A dermatoscopic image of a skin lesion.
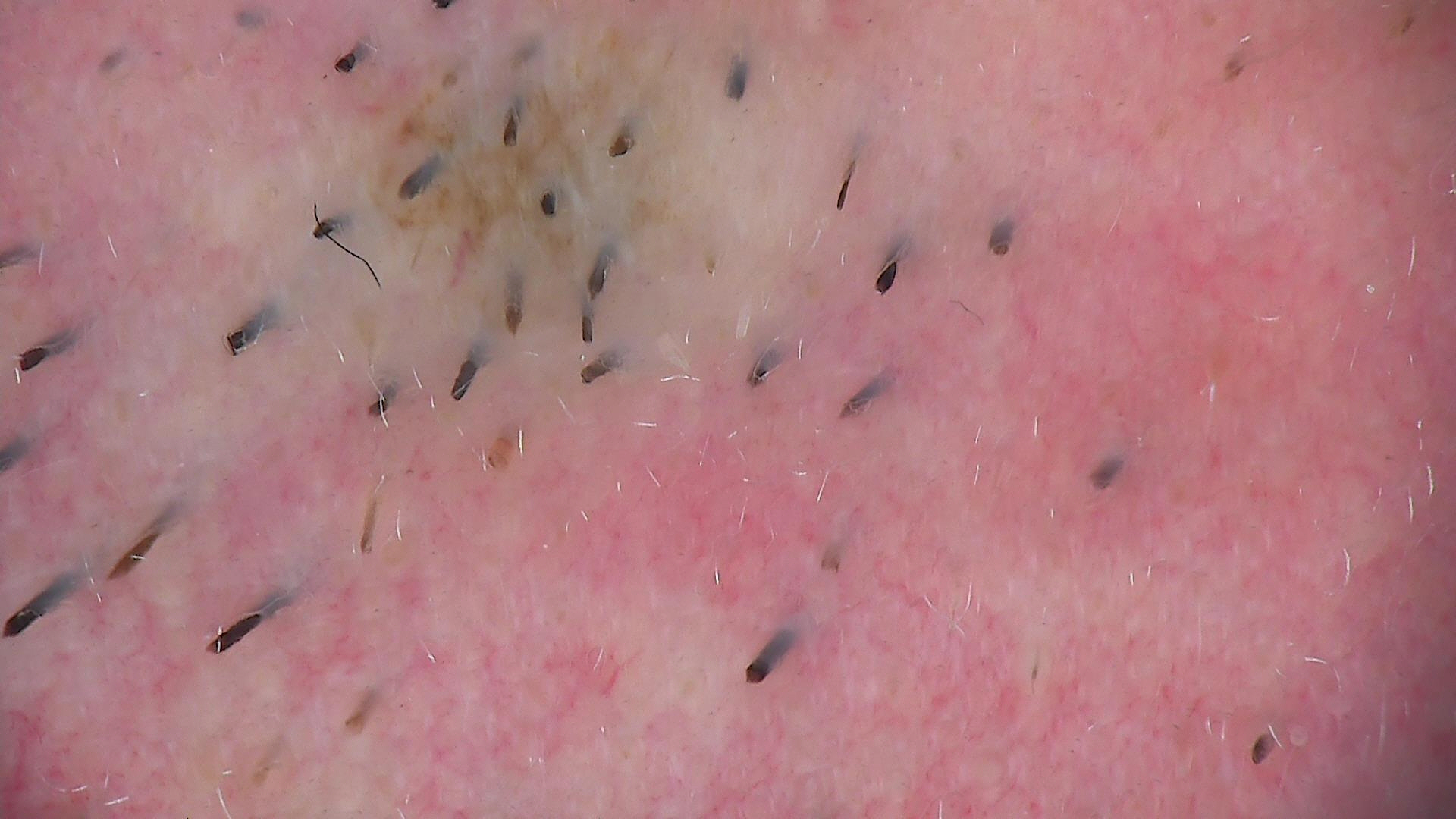<case>
<diagnosis>
<name>Miescher nevus</name>
<code>mcb</code>
<malignancy>benign</malignancy>
<super_class>melanocytic</super_class>
<confirmation>expert consensus</confirmation>
</diagnosis>
</case>